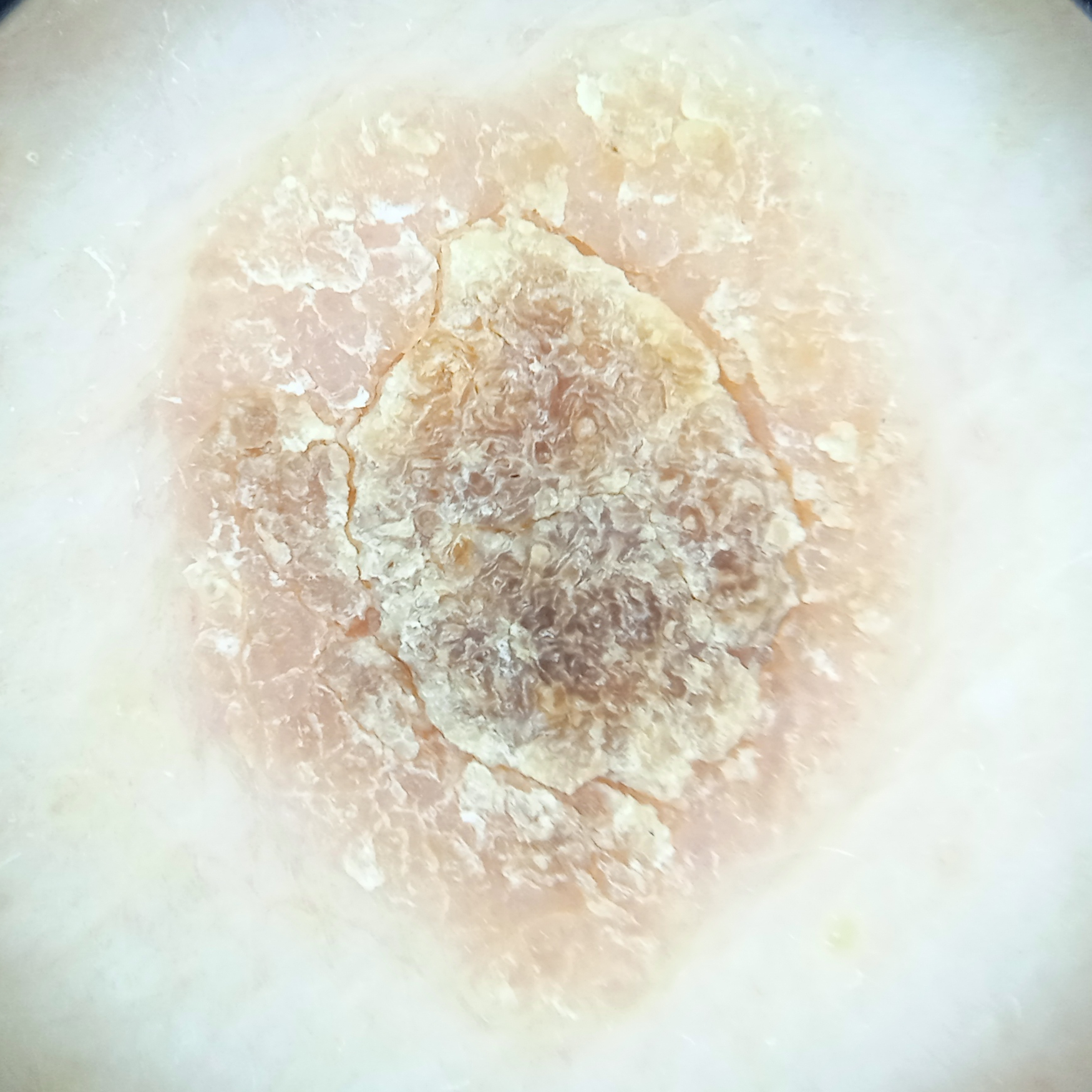Findings: Collected as part of a research study, without a referral diagnosis. The patient says their skin reddens painfully with sun exposure. A dermatoscopic image of a skin lesion. The patient describes having a moderate number of moles. Assessment: Dermatologist review favored a seborrheic keratosis.